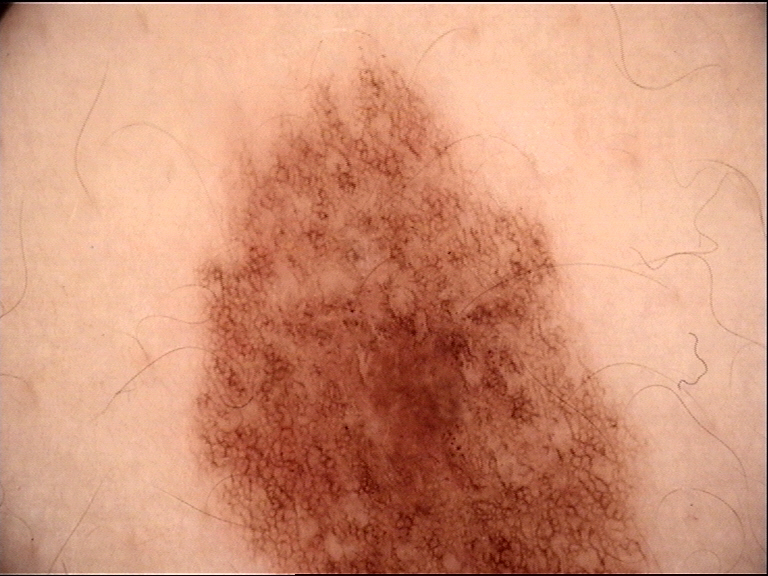Case:
• imaging: dermoscopy
• label: dysplastic junctional nevus (expert consensus)